The chart records alcohol use, prior skin cancer (patient or family), tobacco use, and no pesticide exposure; a clinical photograph of a skin lesion; a male subject in their early 80s; the patient was assessed as skin type II — 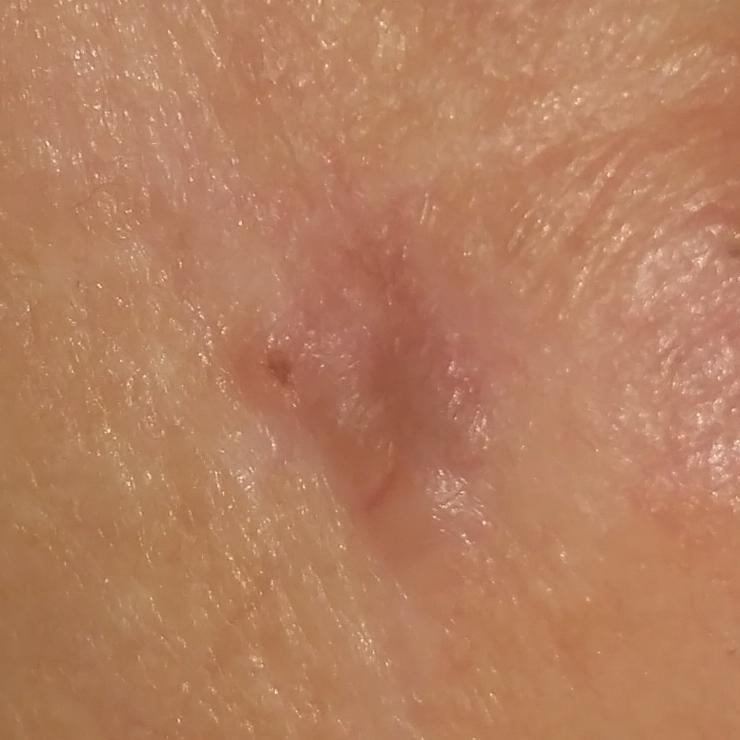Q: Where on the body is the lesion?
A: the face
Q: Lesion size?
A: 6 × 3 mm
Q: What is the diagnosis?
A: basal cell carcinoma (biopsy-proven)